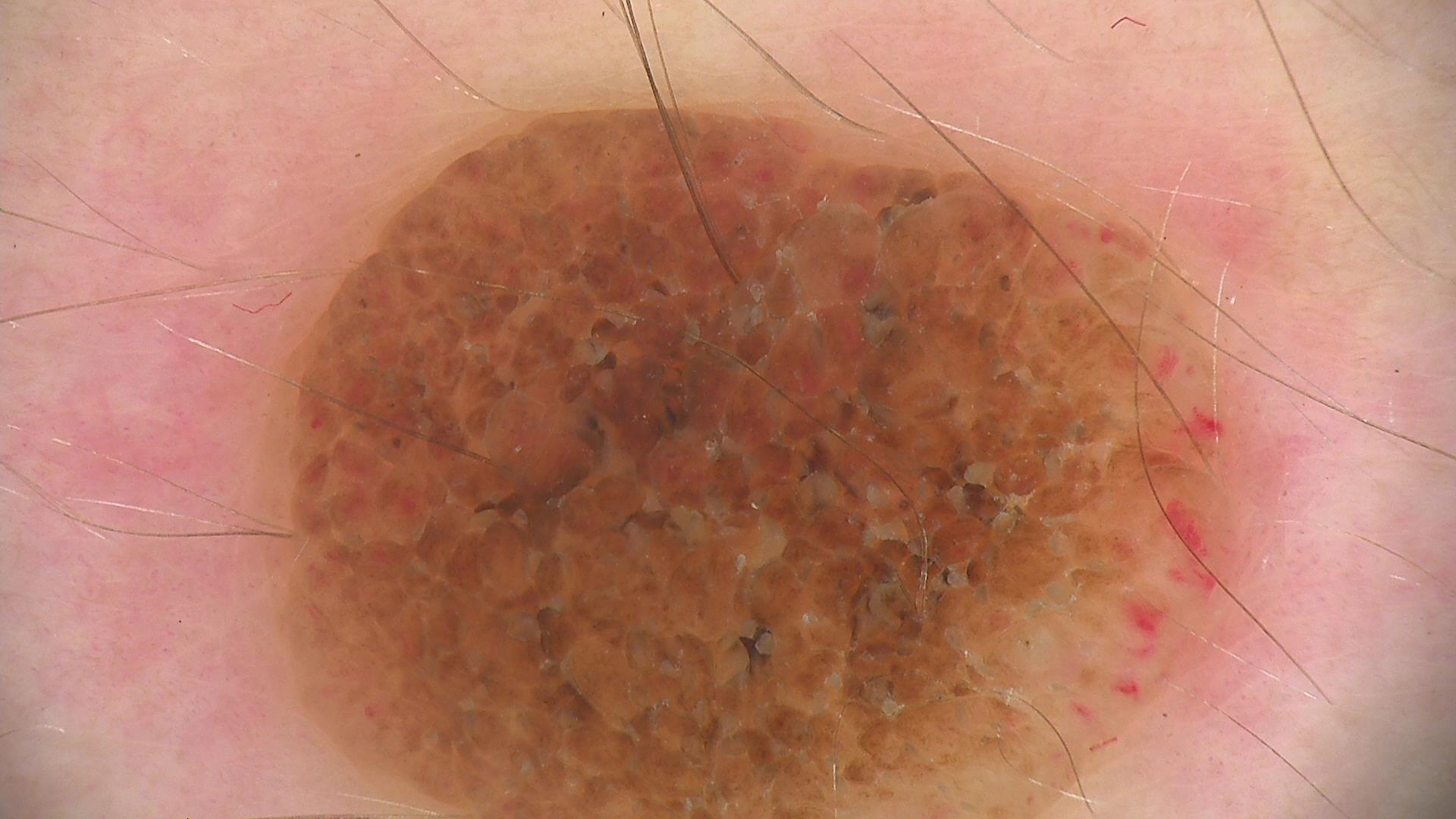• imaging — dermoscopy
• classification — banal
• label — dermal nevus (expert consensus)